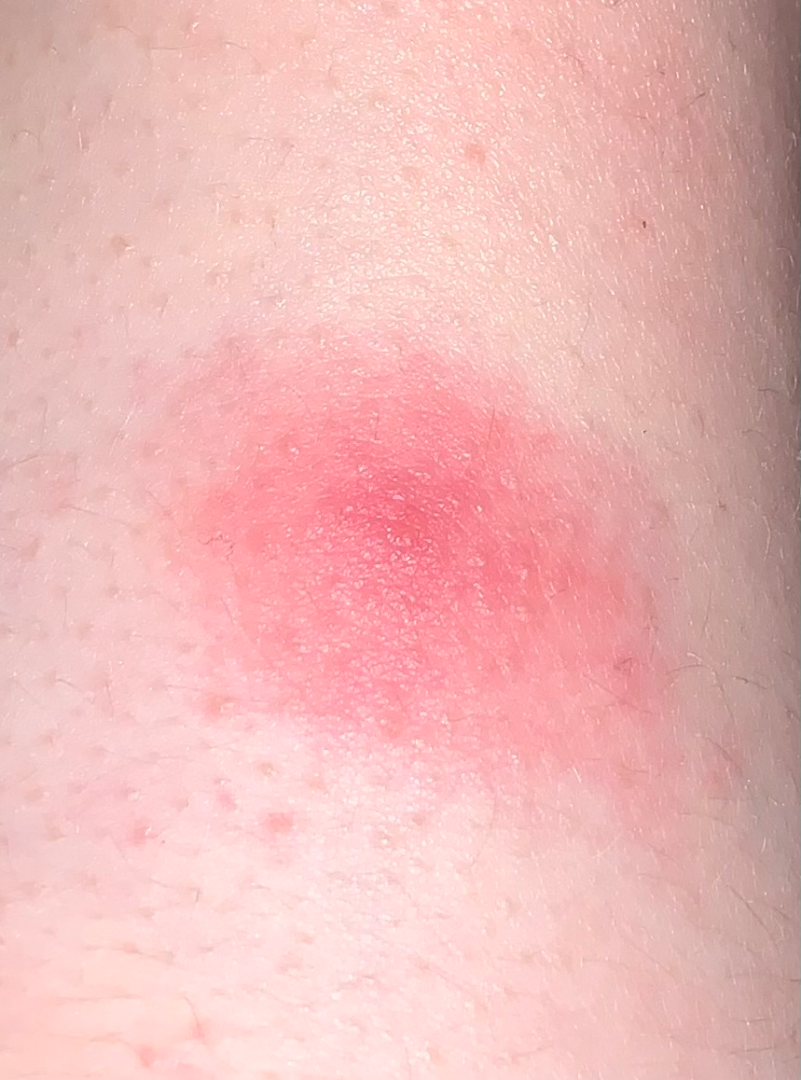• differential · three dermatologists independently reviewed the case: Allergic Contact Dermatitis, Insect Bite, Abscess and Contact dermatitis were each considered, in no particular order